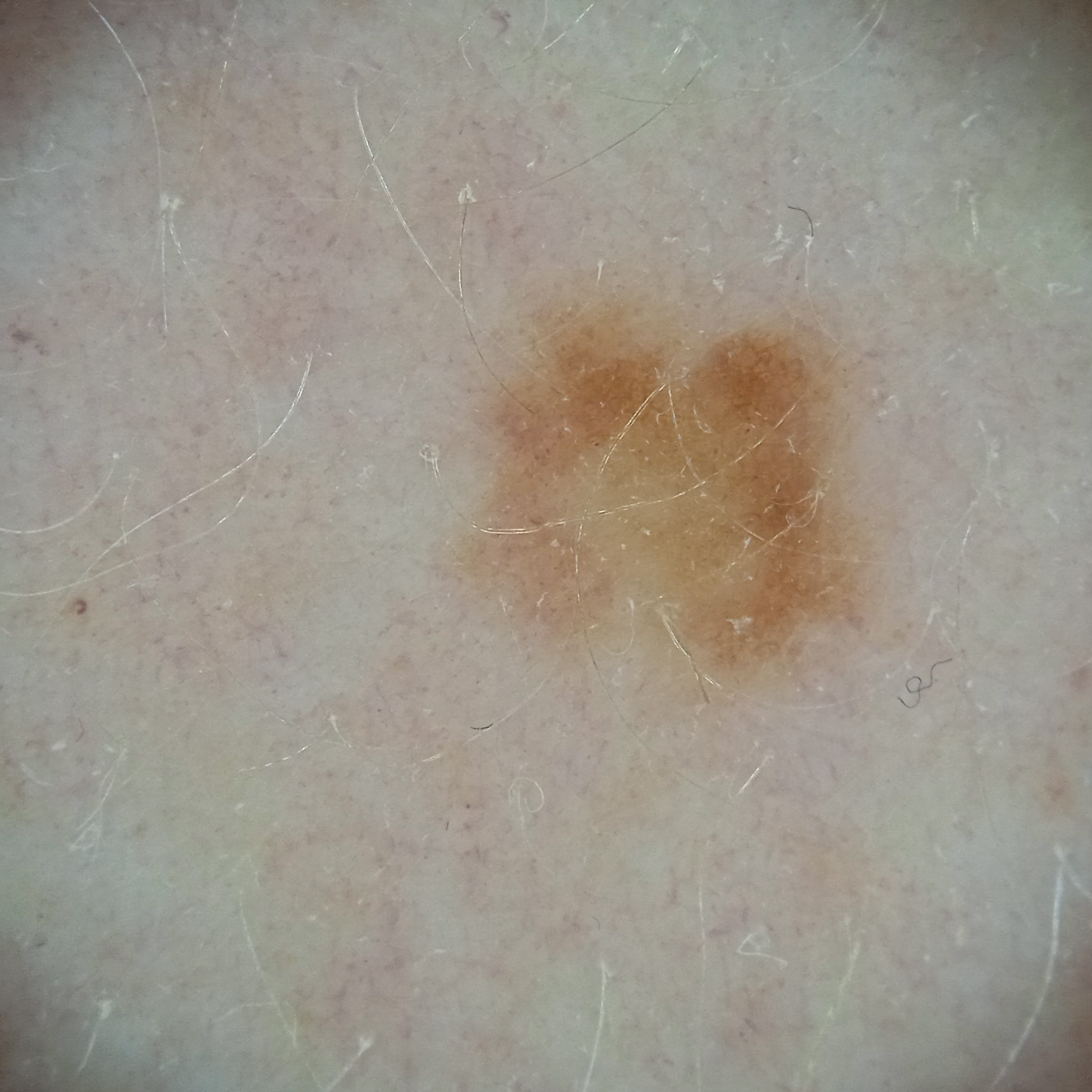assessment: atypical (dysplastic) nevus — dermatologist consensus.